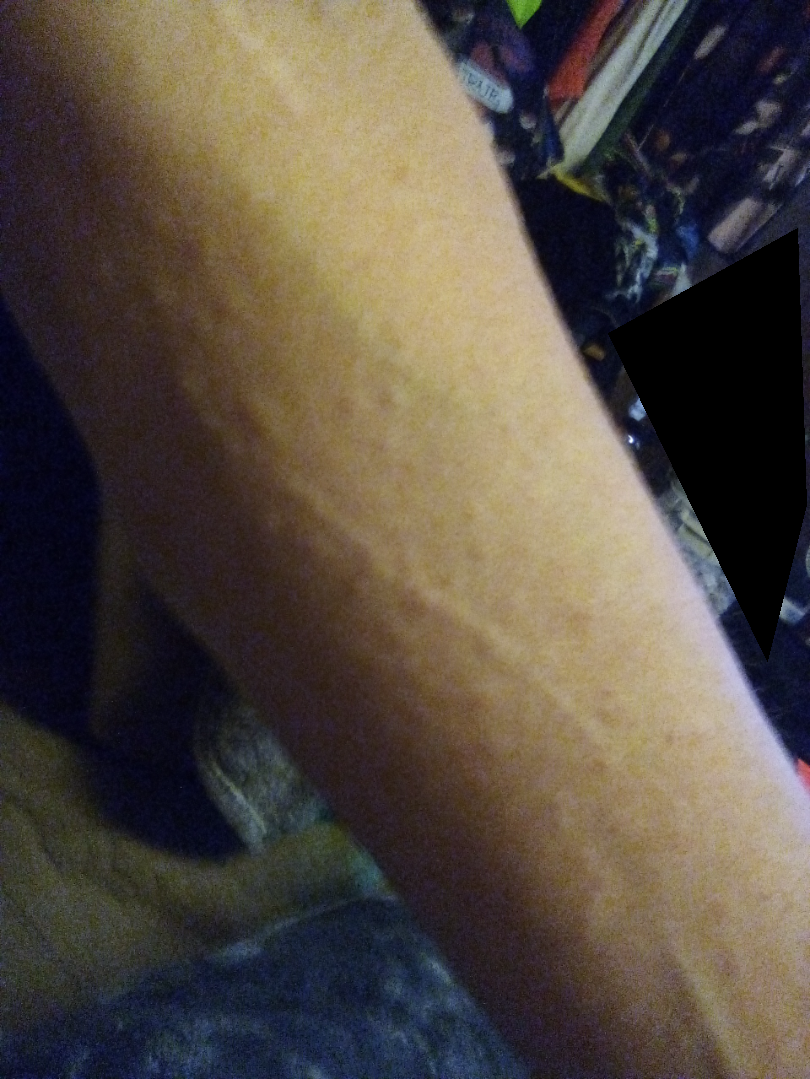Close-up view. On remote dermatologist review, the impression was split between Urticaria and Allergic Contact Dermatitis.